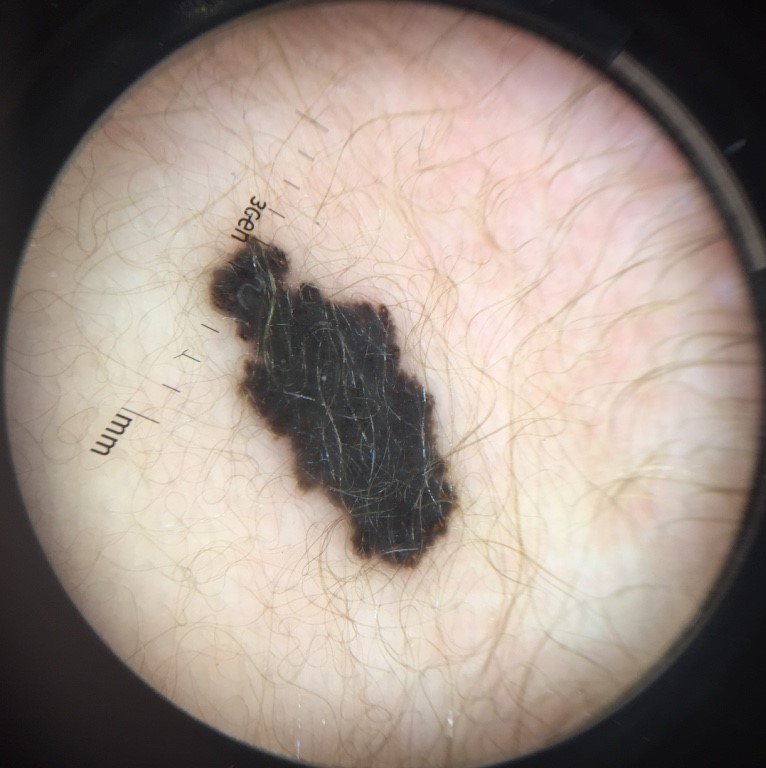class: congenital compound nevus (expert consensus).